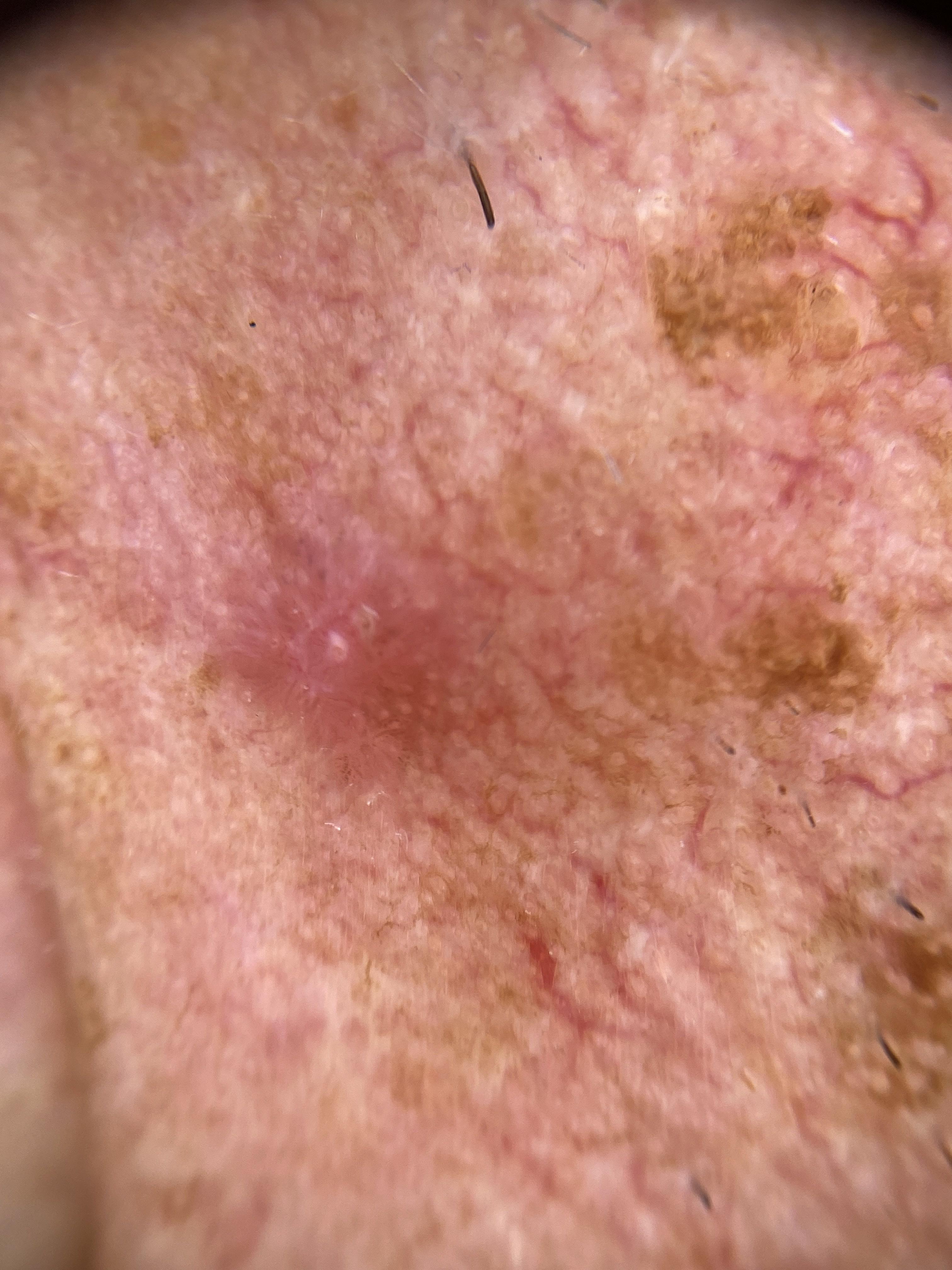Findings:
- modality — dermoscopy
- FST — II
- subject — male, about 85 years old or older
- location — the head or neck
- diagnosis — Basal cell carcinoma (biopsy-proven)